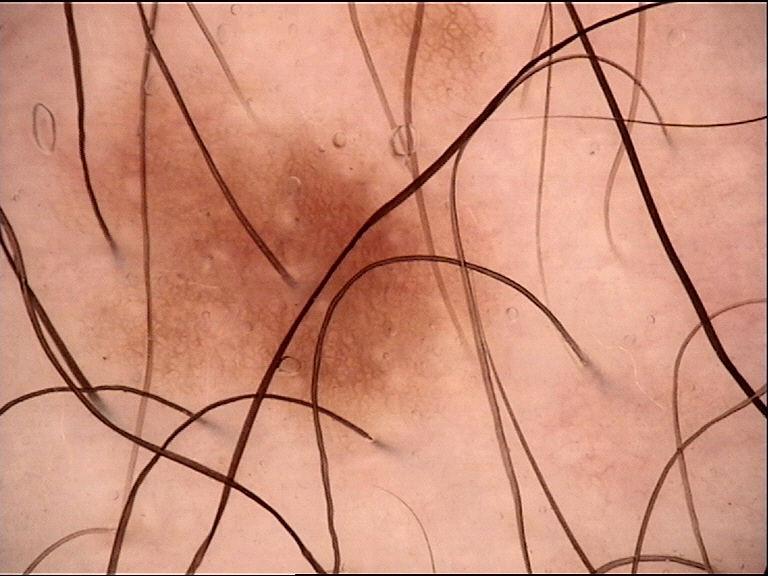diagnostic label = dysplastic junctional nevus (expert consensus).